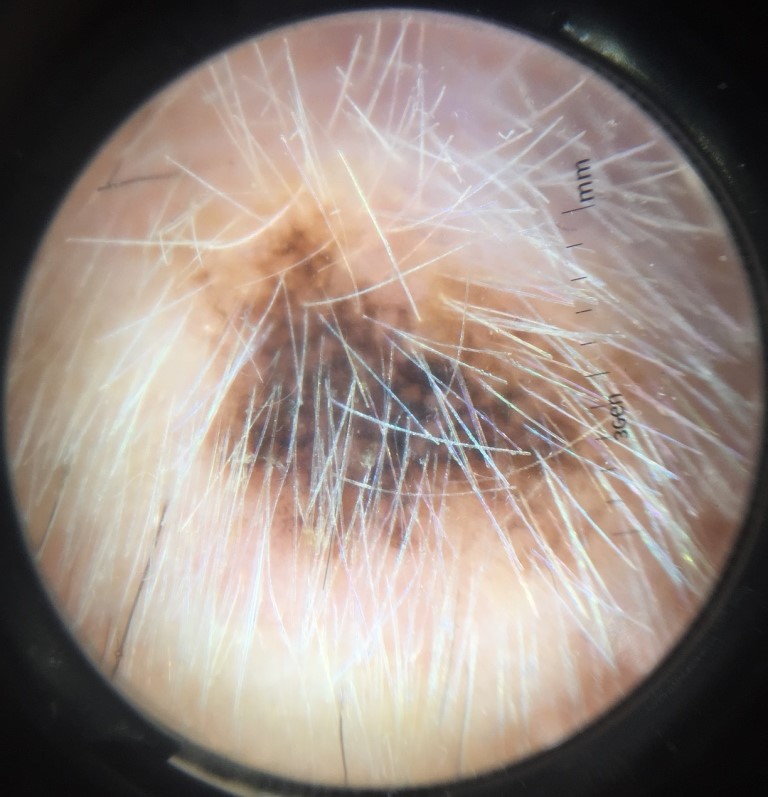Pathology:
The biopsy diagnosis was a melanoma.